A dermoscopic view of a skin lesion — 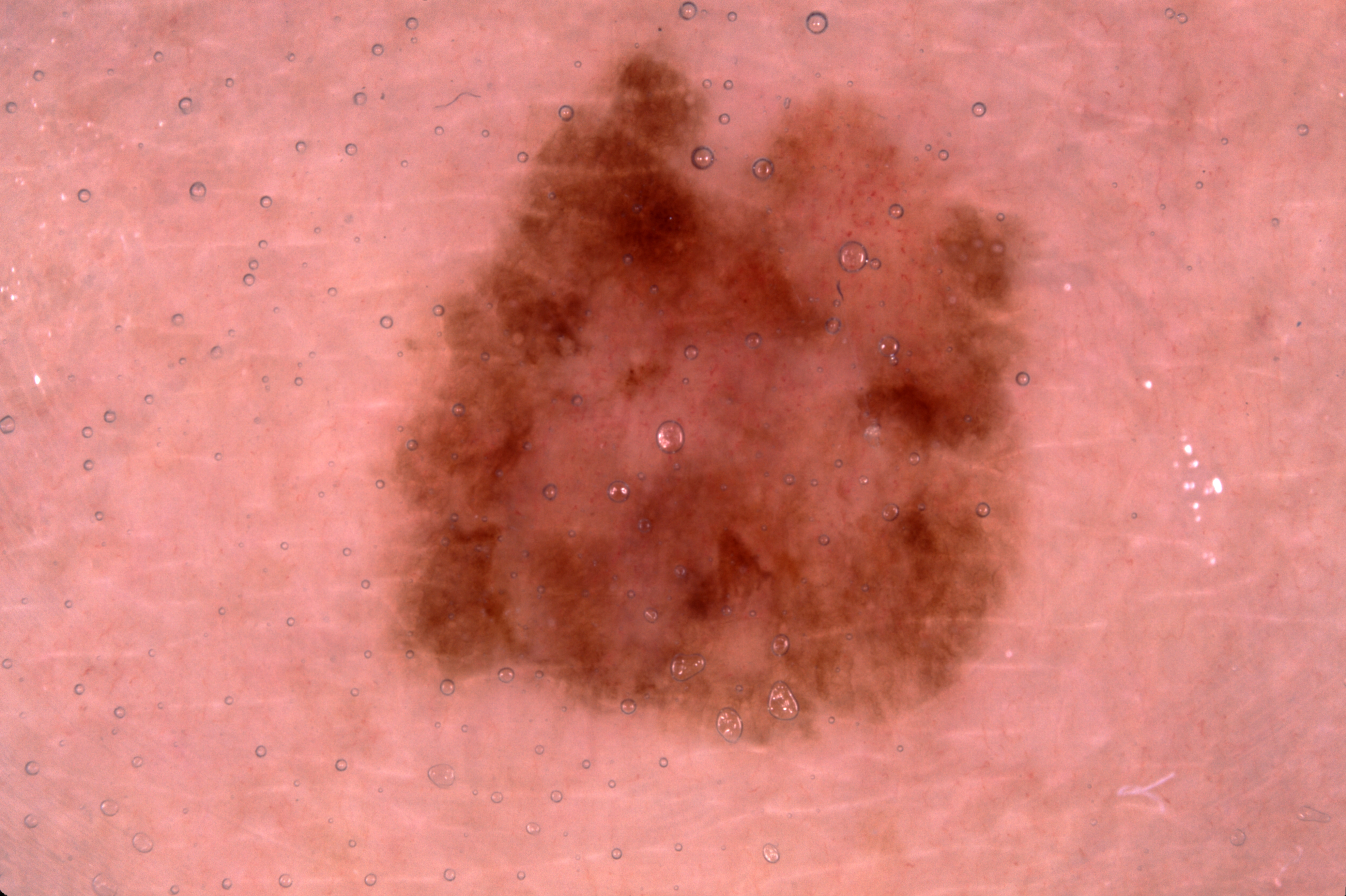The lesion takes up a moderate portion of the field. With coordinates (x1, y1, x2, y2), the lesion occupies the region box(390, 38, 1034, 745). Dermoscopic examination shows pigment network. Biopsy-confirmed as a melanoma.